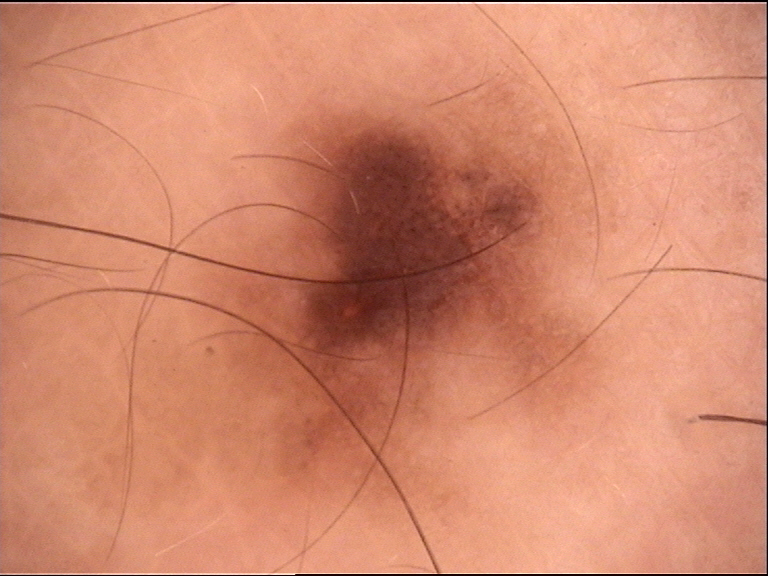  image: dermoscopy
  diagnosis:
    name: dysplastic junctional nevus
    code: jd
    malignancy: benign
    super_class: melanocytic
    confirmation: expert consensus